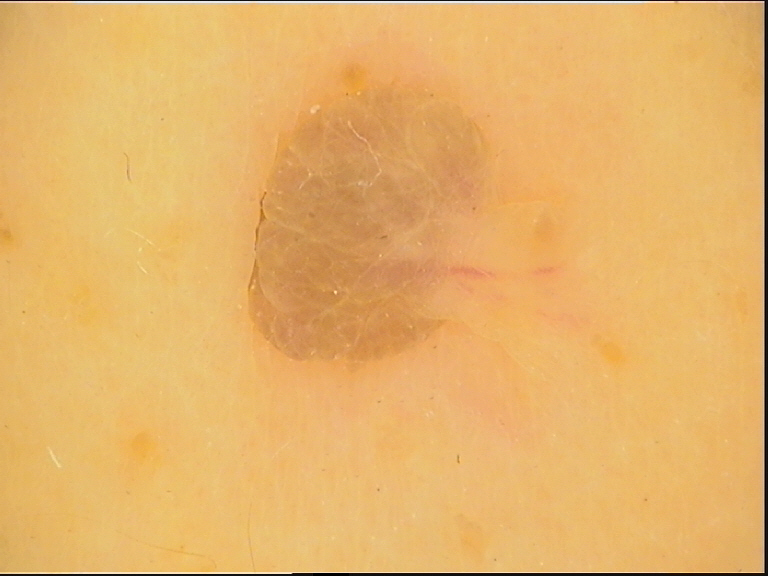Diagnosed as a dermal nevus.